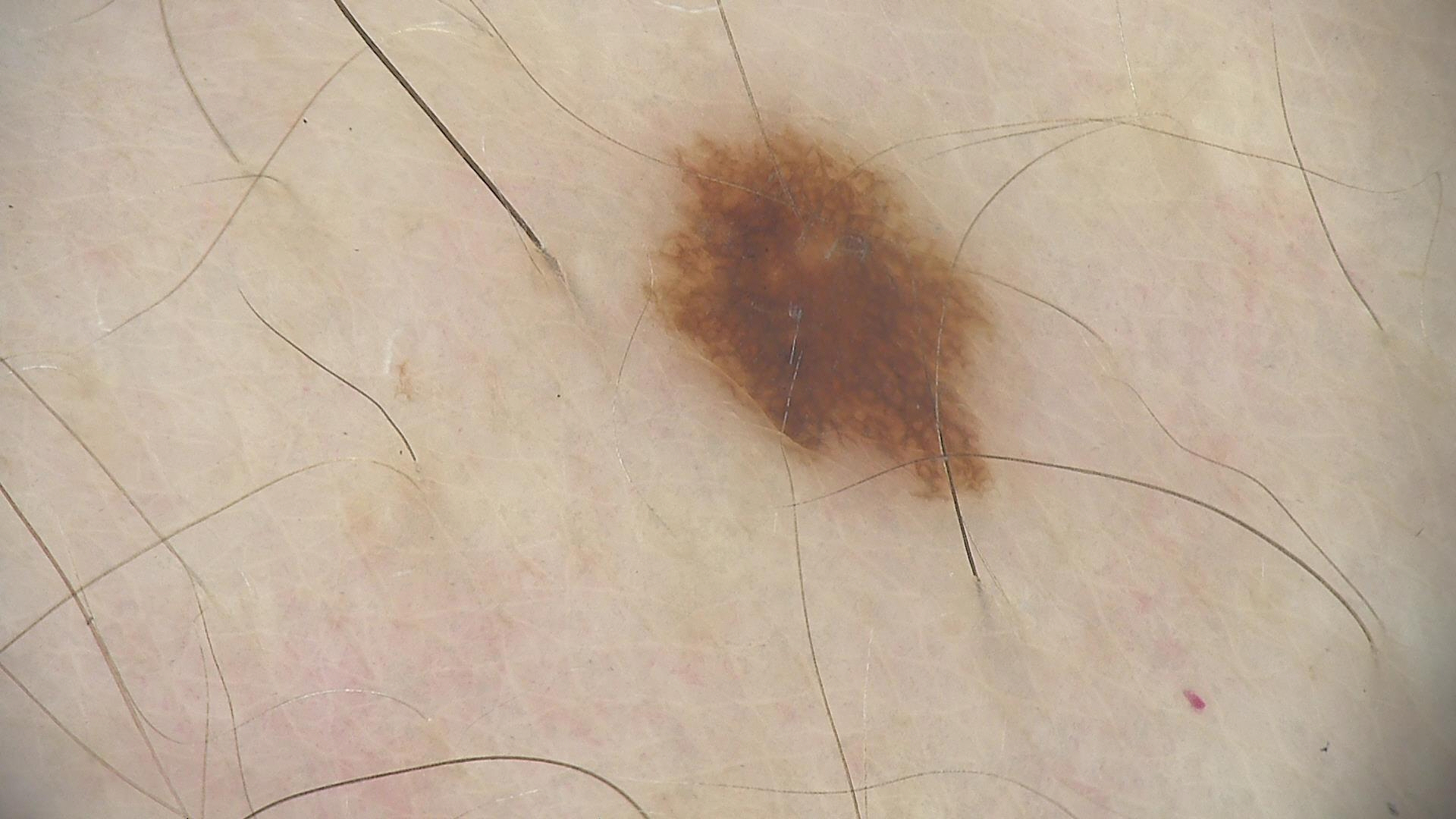imaging — dermatoscopy; assessment — dysplastic junctional nevus (expert consensus).